A clinical photo of a skin lesion taken with a smartphone. A male patient aged 64. The chart records pesticide exposure and alcohol use. Recorded as Fitzpatrick skin type III: 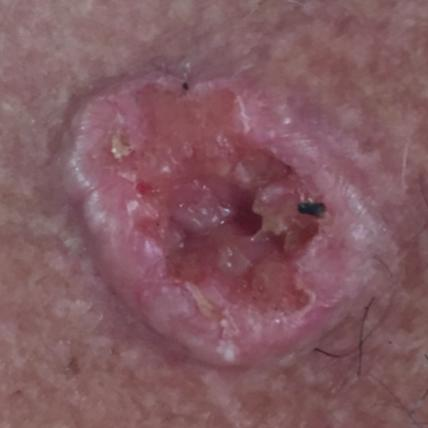Case summary: The lesion measures approximately 20 × 14 mm. Per patient report, the lesion itches, hurts, has bled, is elevated, and has grown. Conclusion: Biopsy-confirmed as a basal cell carcinoma.